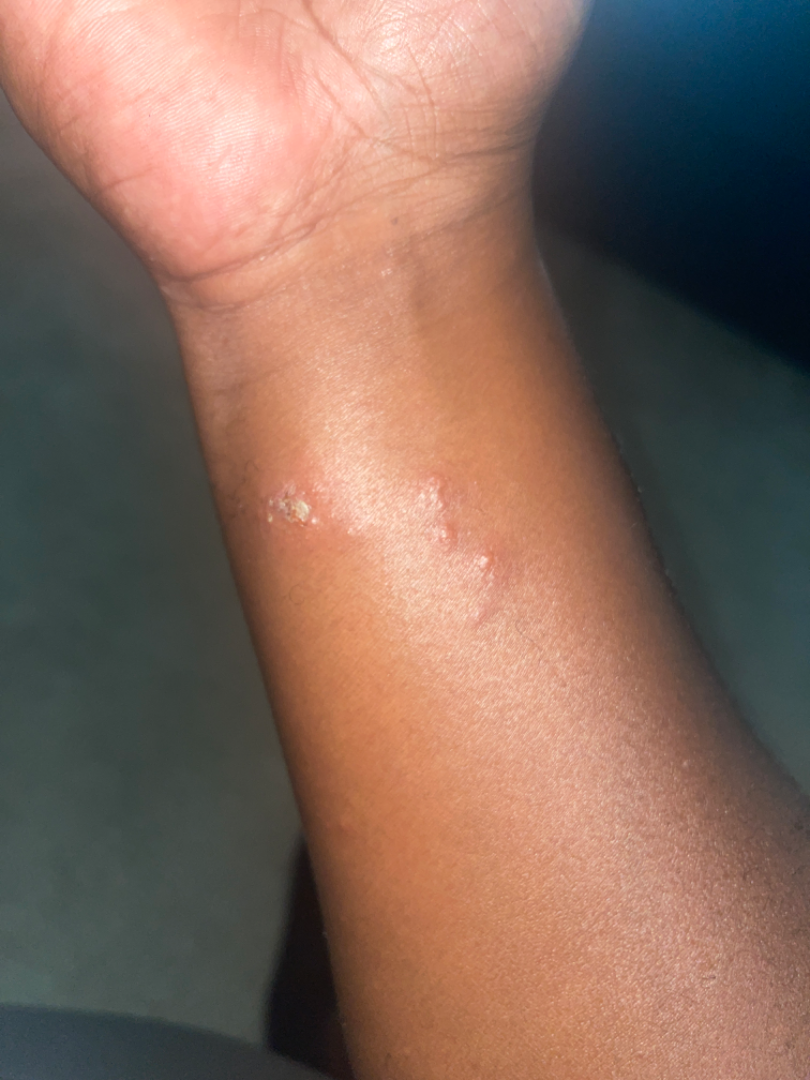patient = male, age 40–49 | patient describes the issue as = a rash | described texture = raised or bumpy, fluid-filled and rough or flaky | photo taken = close-up | onset = less than one week | lesion symptoms = itching, bothersome appearance and enlargement | differential diagnosis = single-reviewer assessment: Scabies and Molluscum Contagiosum were considered with similar weight; less likely is Perforating dermatosis.